Dermoscopy of a skin lesion.
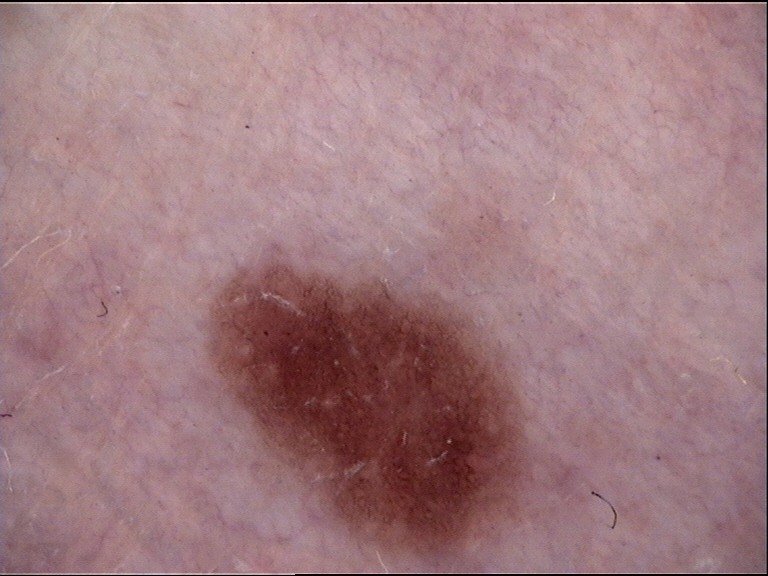The diagnostic label was a benign lesion — a dysplastic junctional nevus.